Symptoms reported: bothersome appearance, the affected area is the front of the torso, the photograph was taken at an angle, texture is reported as flat: 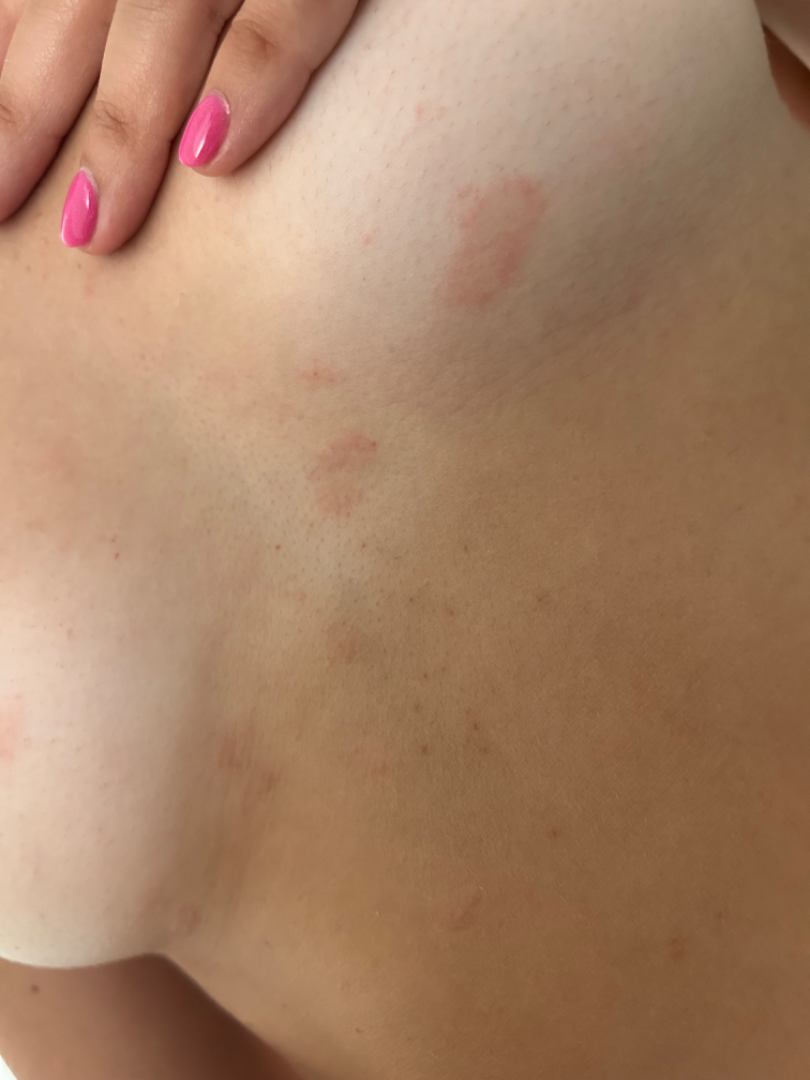Assessment: The skin findings could not be characterized from the image.